No relevant systemic symptoms, reported duration is less than one week, an image taken at a distance, texture is reported as flat, the affected area is the arm, symptoms reported: darkening: 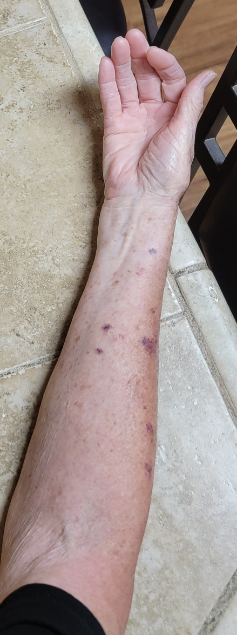  differential:
    leading:
      - ecchymoses